A male subject aged around 20; a dermoscopic image of a skin lesion:
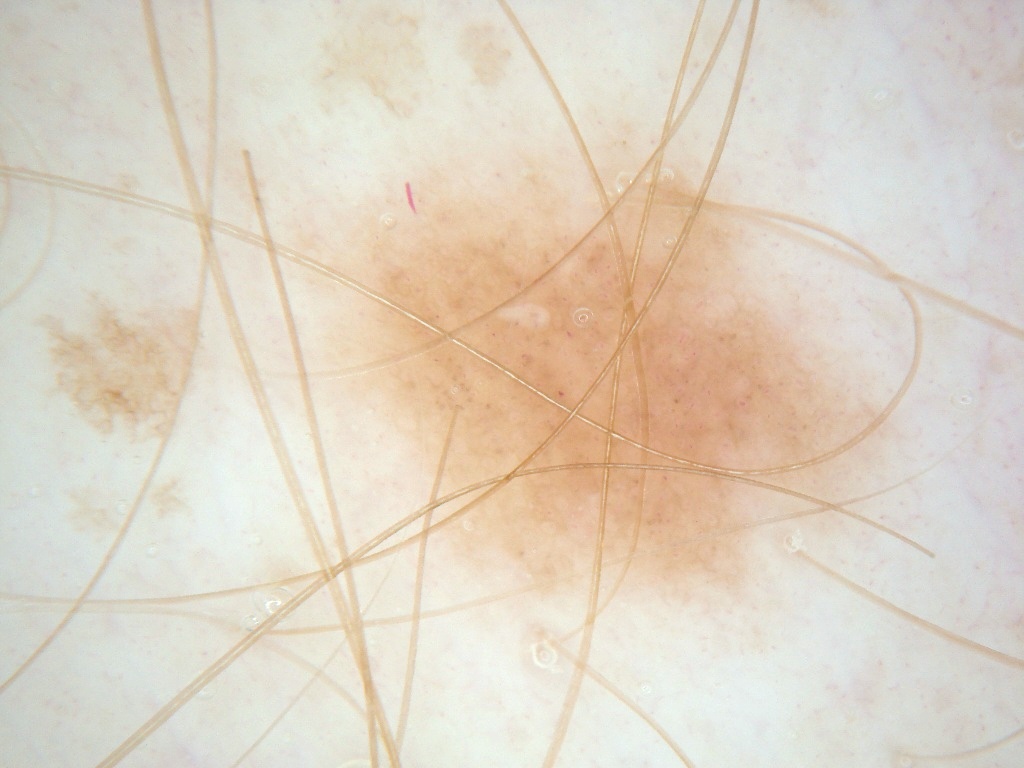lesion bbox — 292/121/927/647; absent dermoscopic findings — negative network, pigment network, globules, streaks, and milia-like cysts; assessment — a melanocytic nevus.